Dermoscopy of a skin lesion: 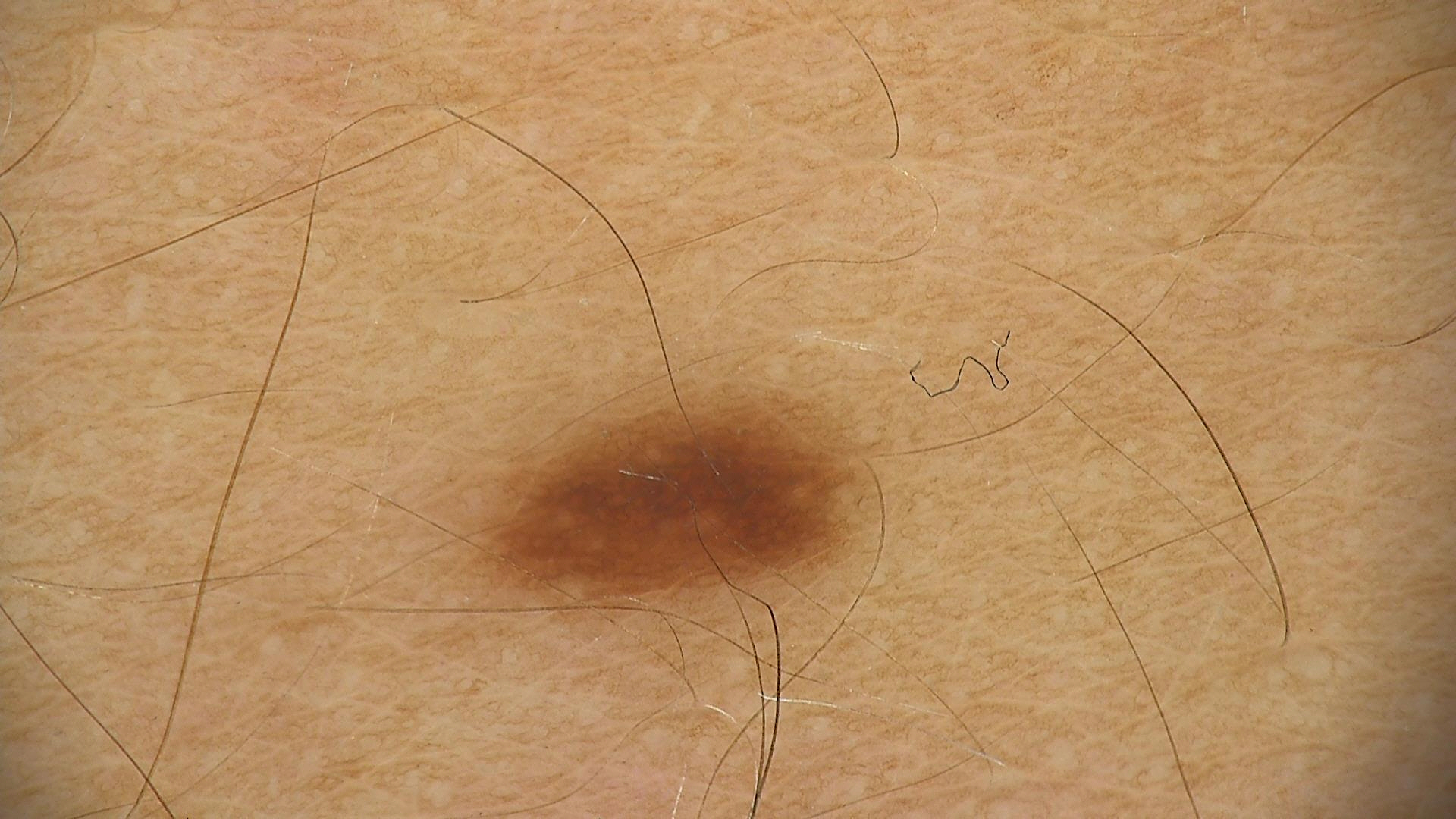– subtype · banal
– label · junctional nevus (expert consensus)